This image was taken at a distance · the affected area is the arm.
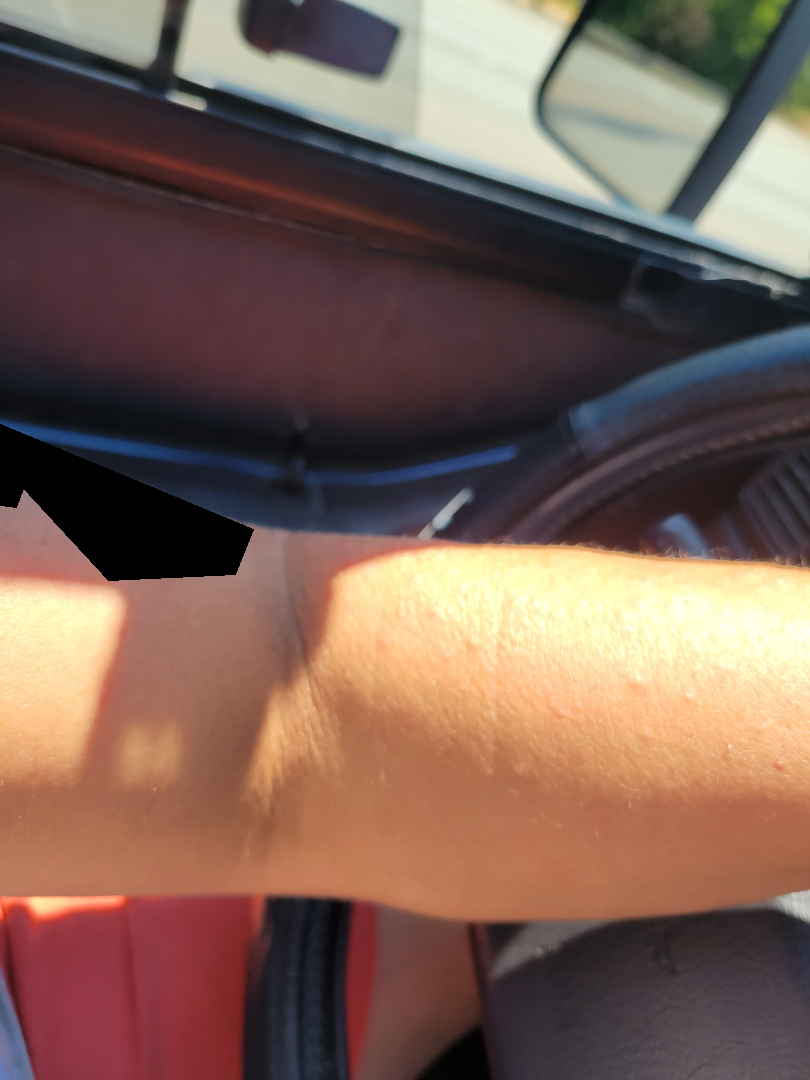<report>
  <assessment>could not be assessed</assessment>
</report>